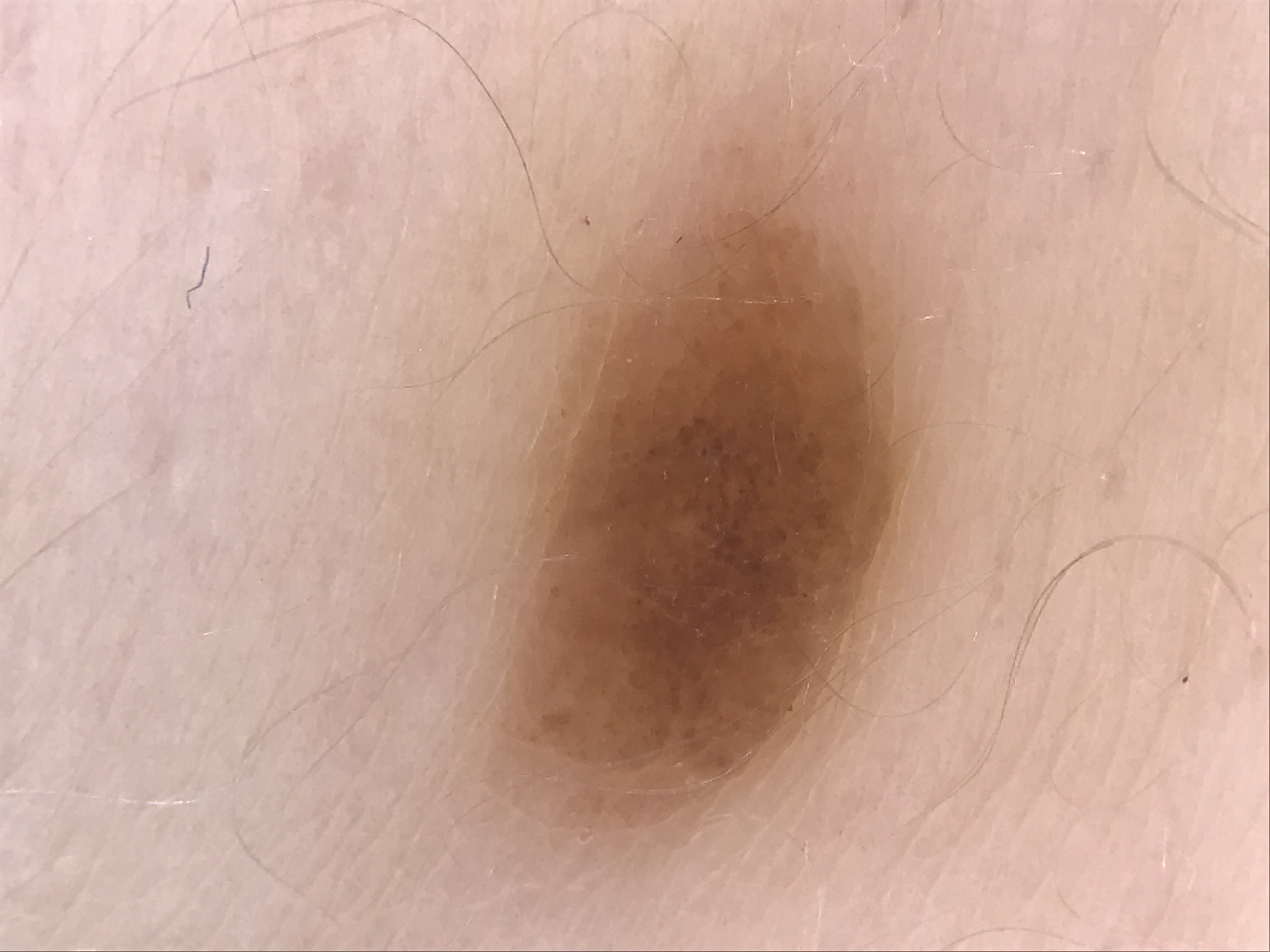image type: dermoscopy, classification: keratinocytic, label: seborrheic keratosis (expert consensus).